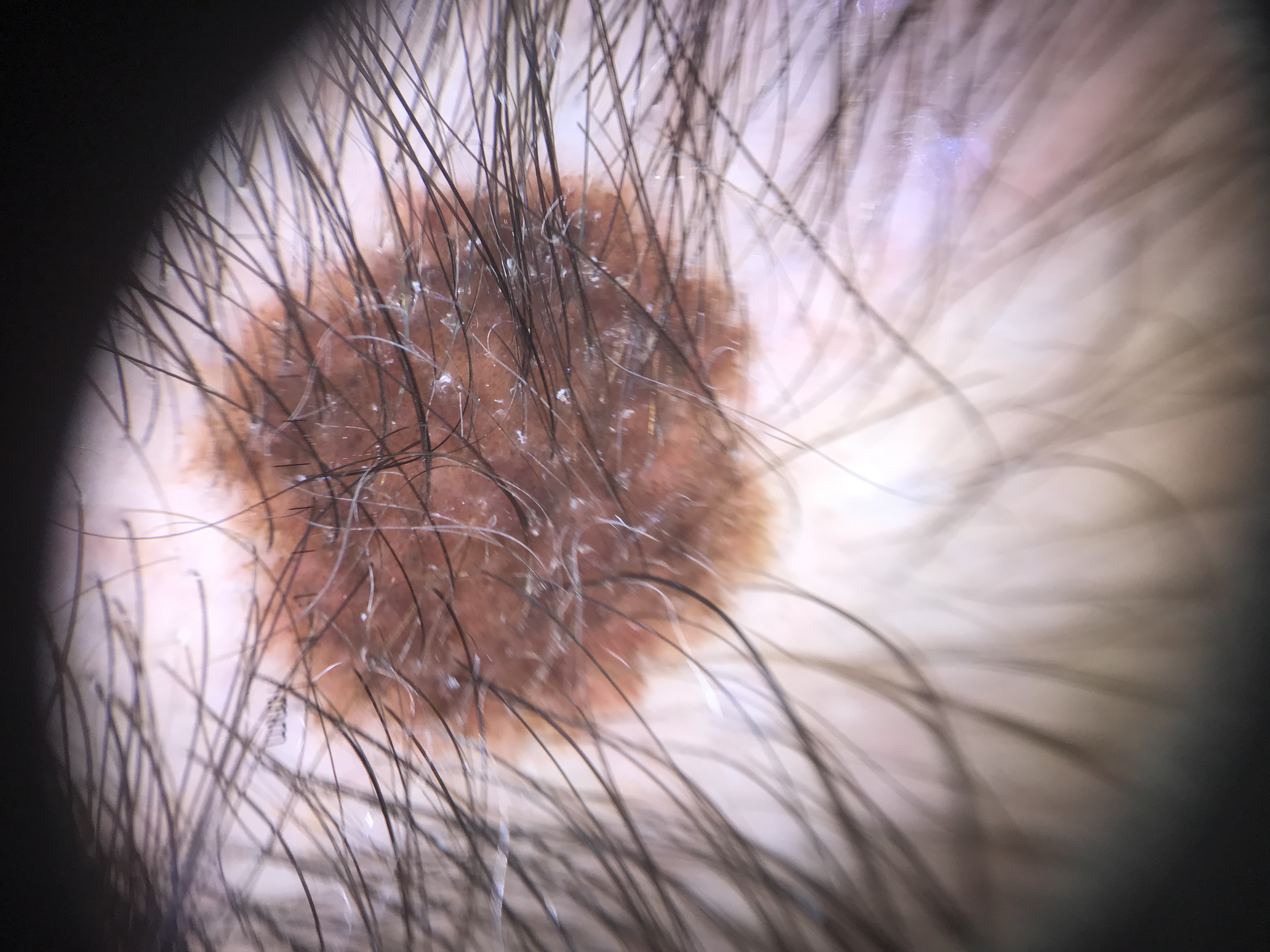A dermoscopic image of a skin lesion. The diagnosis was a congenital compound nevus.